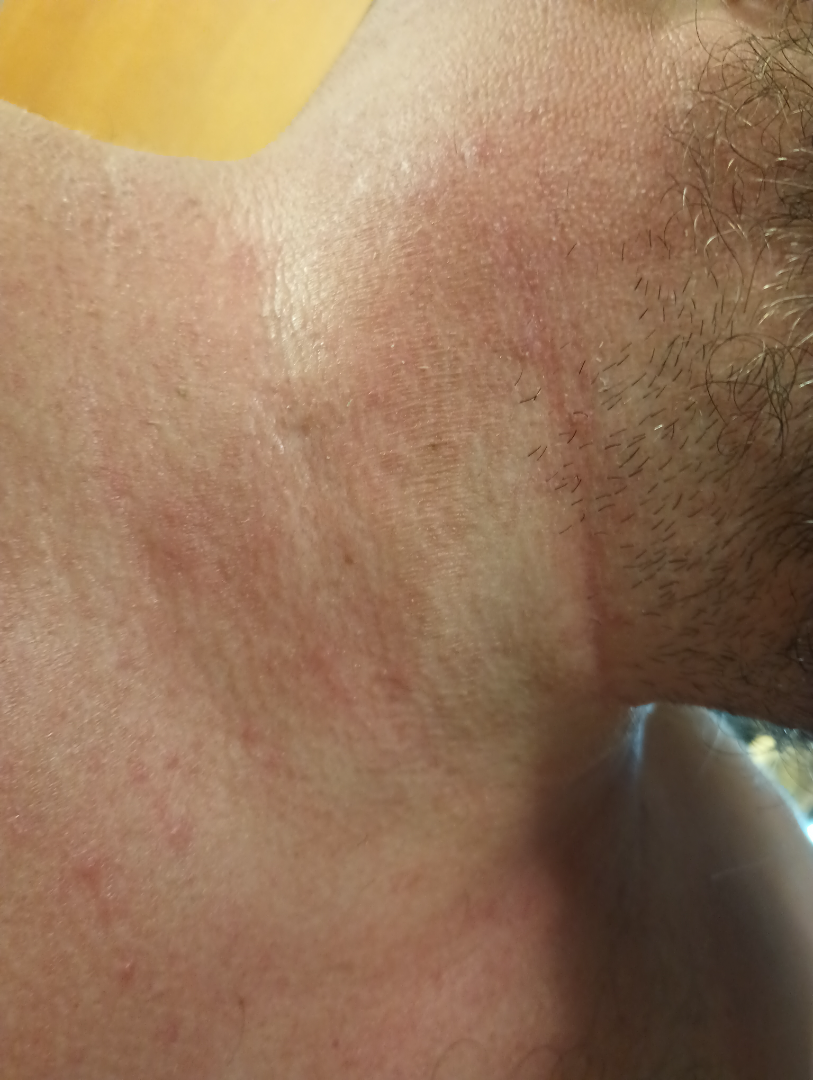  symptoms:
    - itching
    - pain
    - bothersome appearance
    - burning
  shot_type: close-up
  body_site:
    - front of the torso
    - head or neck
  patient_category: a rash
  duration: less than one week
  differential:
    leading:
      - Irritant Contact Dermatitis
    considered:
      - Allergic Contact Dermatitis